A dermoscopic photograph of a skin lesion.
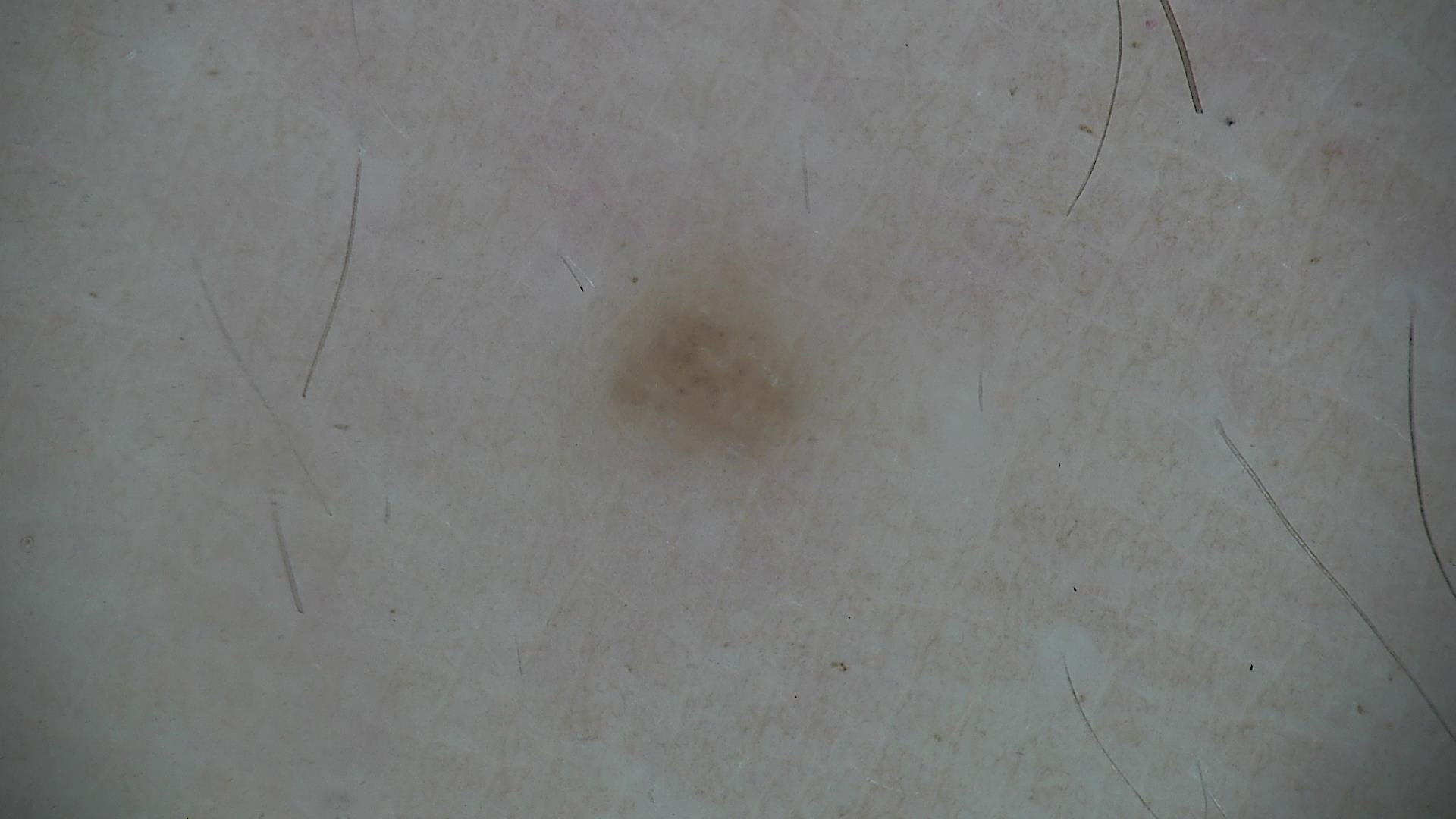class = dysplastic junctional nevus (expert consensus).